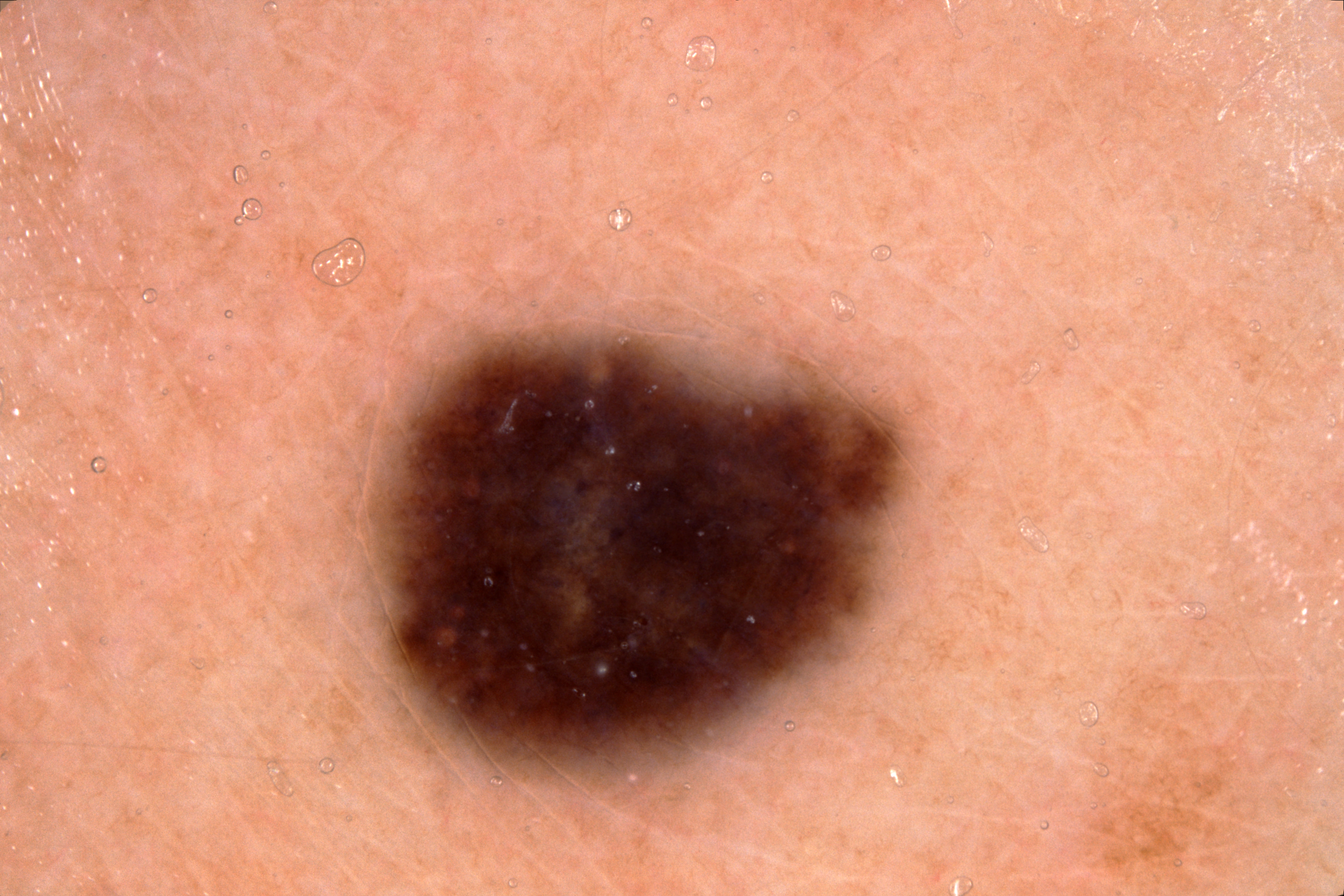A dermatoscopic image of a skin lesion.
A female subject in their mid-30s.
In (x1, y1, x2, y2) order, the lesion is located at 326/293/931/823.
On dermoscopy, the lesion shows milia-like cysts.
Clinically diagnosed as a melanocytic nevus, a benign skin lesion.